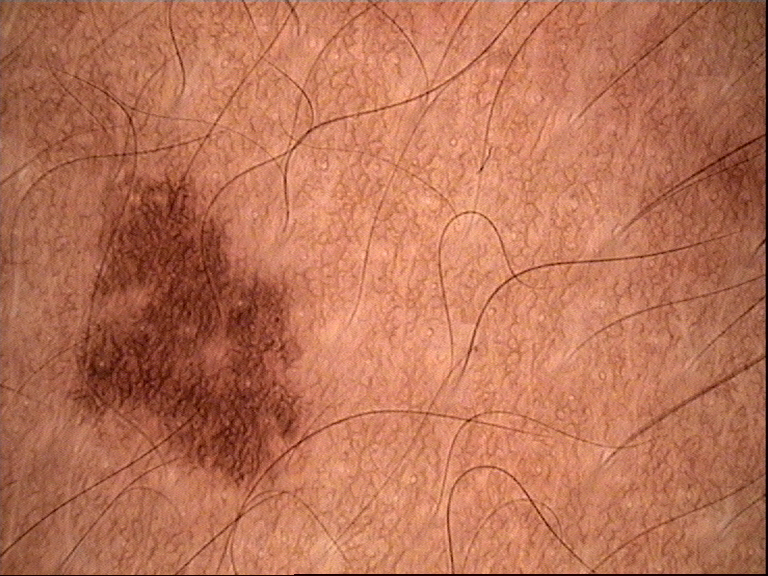Findings:
• diagnostic label · dysplastic junctional nevus (expert consensus)